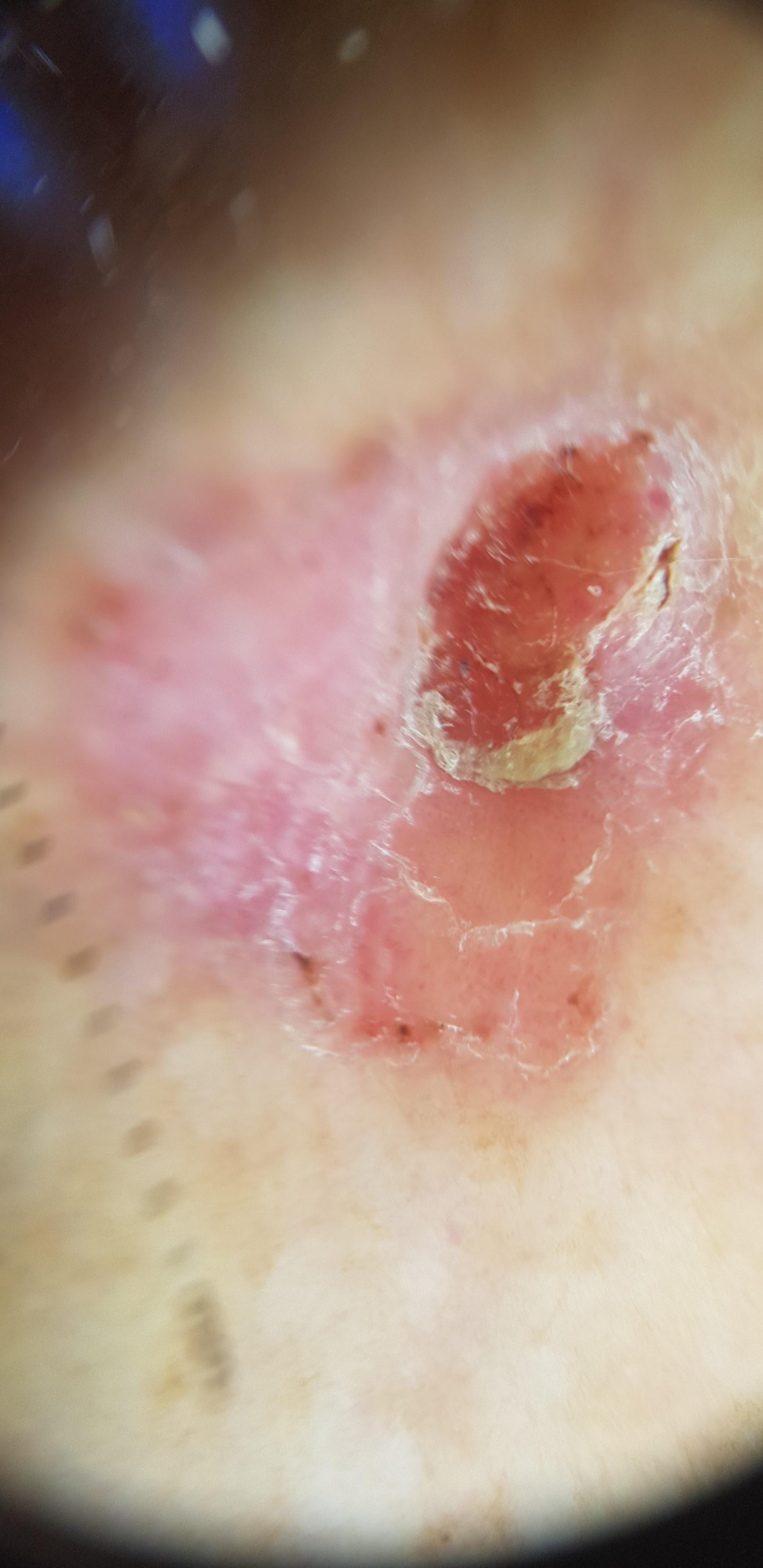Q: What is this lesion?
A: Basal cell carcinoma (biopsy-proven)